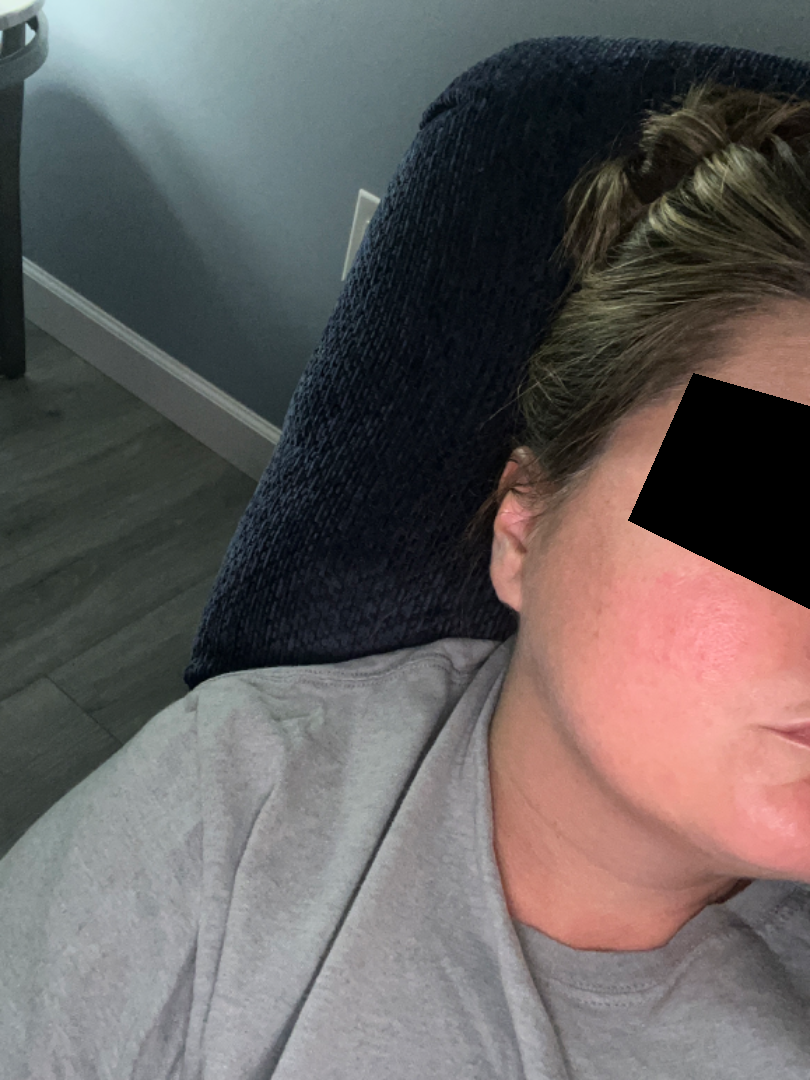Patient information: Located on the head or neck. The patient notes bothersome appearance. Reported duration is about one day. Self-categorized by the patient as skin that appeared healthy to them. The photograph was taken at a distance. Skin tone: Fitzpatrick II; human graders estimated 2 on the Monk skin tone scale. The lesion is described as raised or bumpy. Review: One reviewing dermatologist: the differential, in no particular order, includes Rosacea and Flushing; a remote consideration is Cutaneous lupus.